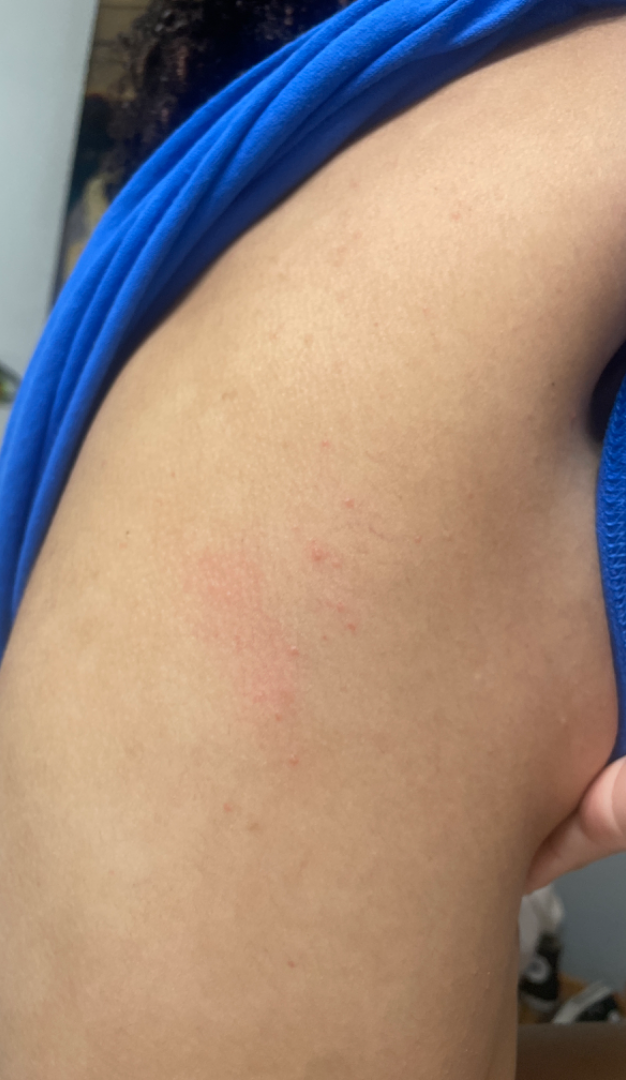Impression: The dermatologist could not determine a likely condition from the photograph alone.